A clinical photograph of a skin lesion — 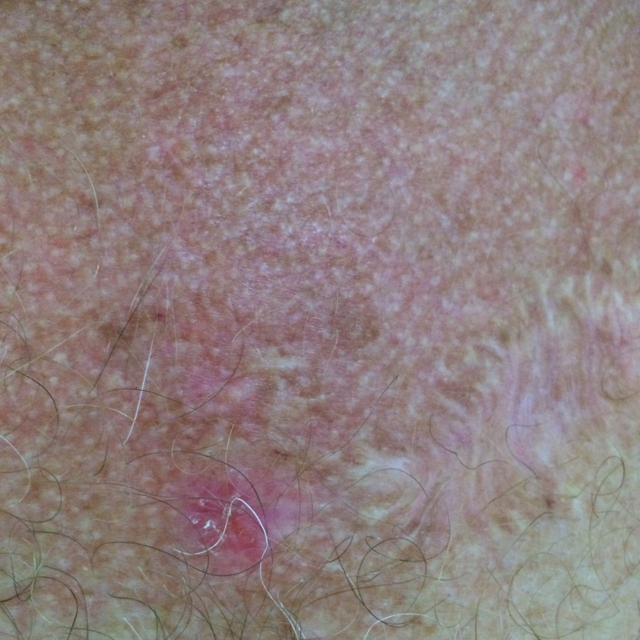{"lesion_location": "the chest", "symptoms": {"present": ["itching"]}, "diagnosis": {"name": "actinic keratosis", "code": "ACK", "malignancy": "indeterminate", "confirmation": "clinical consensus"}}